The palm and arm are involved, this is a close-up image — 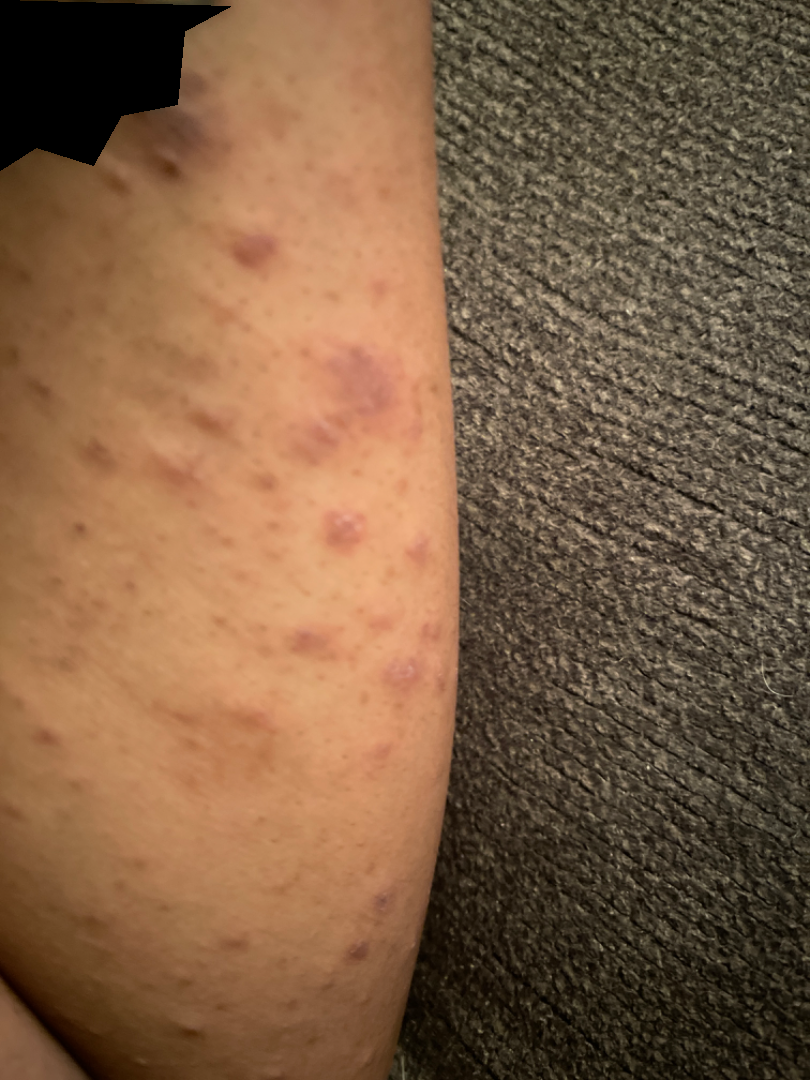Assessment:
On dermatologist assessment of the image: Pityriasis lichenoides (weight 0.67); Psoriasis (weight 0.33).